An image taken at an angle; the lesion involves the front of the torso; the contributor notes the lesion is raised or bumpy; no relevant systemic symptoms; the contributor notes itching and burning; the patient is a female aged 70–79; self-categorized by the patient as a rash — 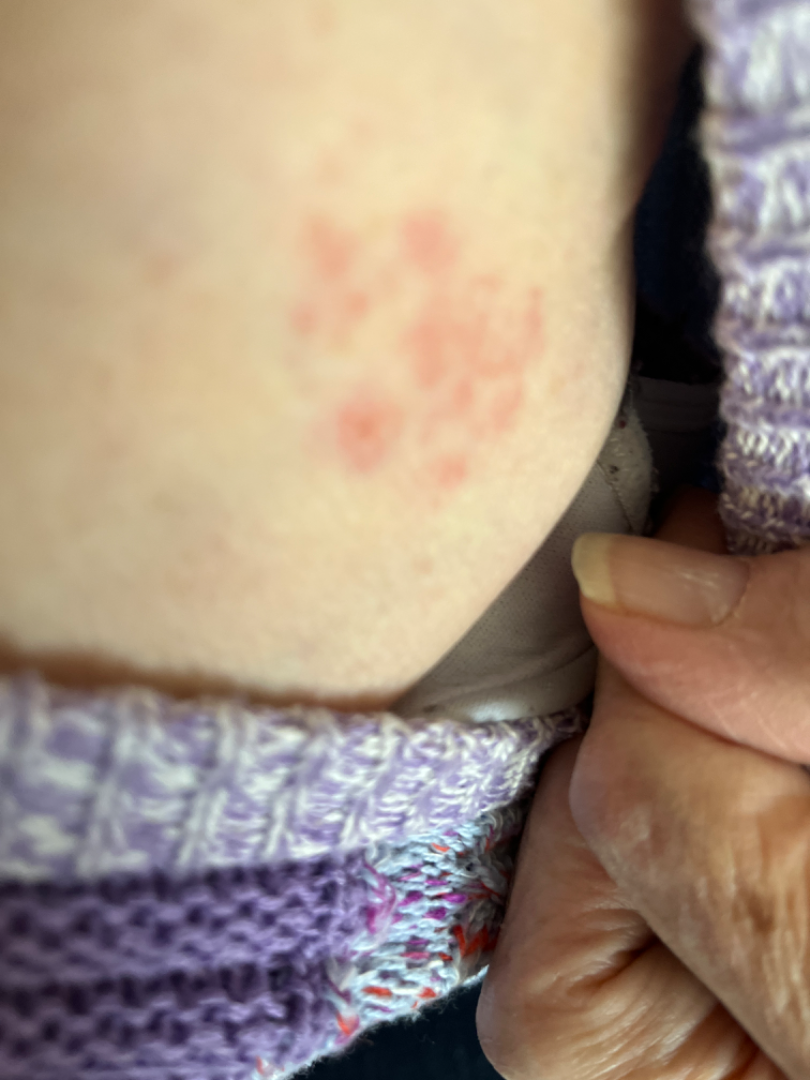Insect Bite (possible); Allergic Contact Dermatitis (possible); Herpes Simplex (possible).